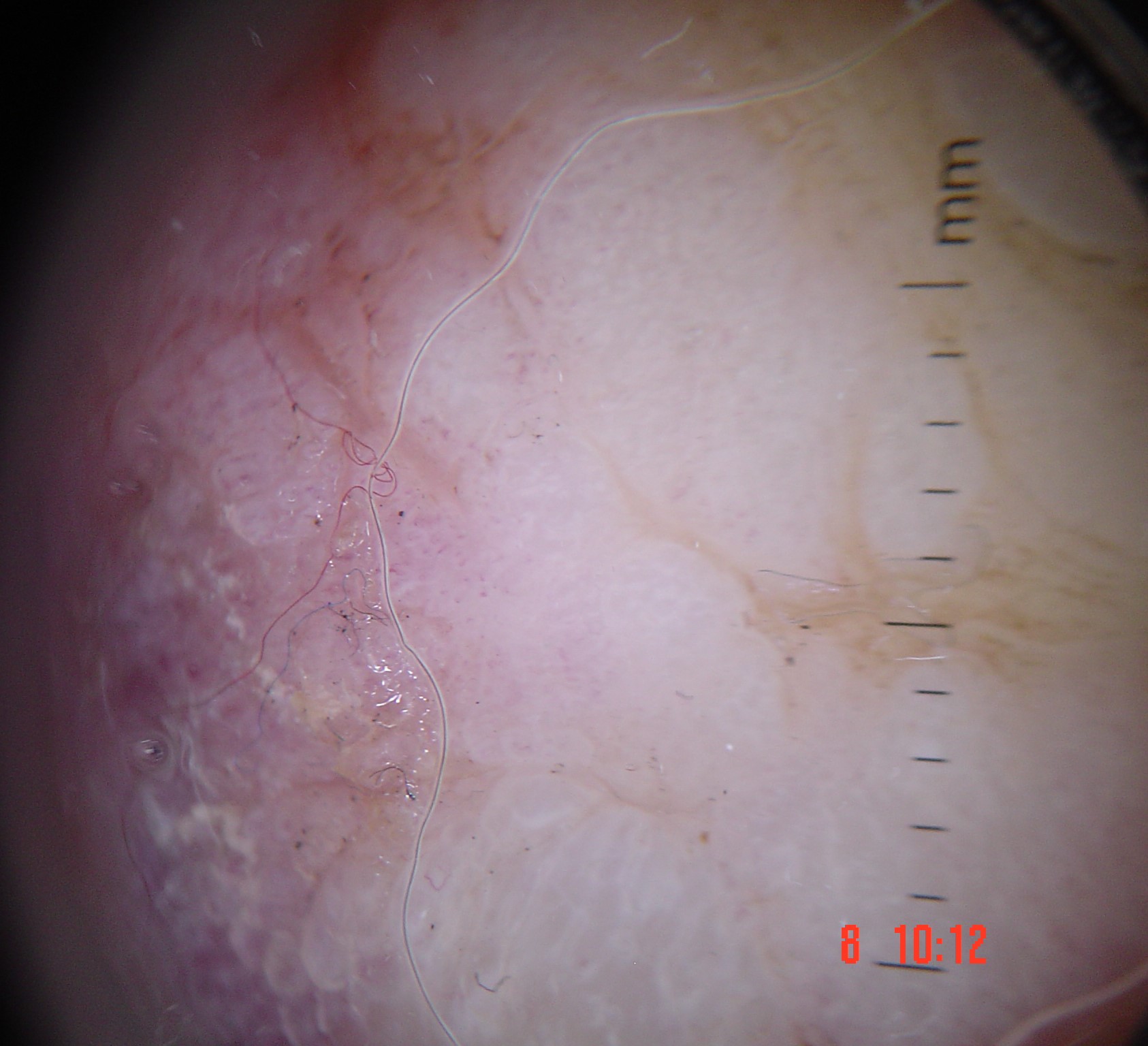image type = dermatoscopy | diagnosis = acral nodular melanoma (biopsy-proven).